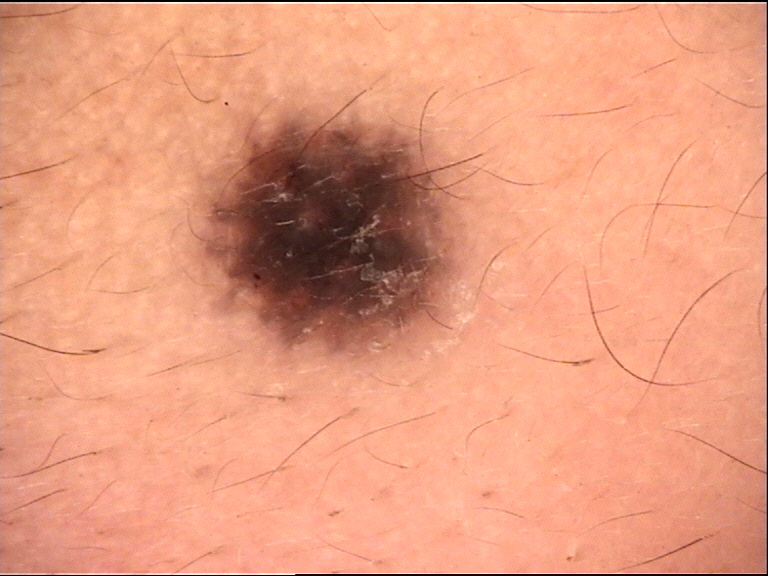Conclusion:
Consistent with a banal lesion — a compound nevus.